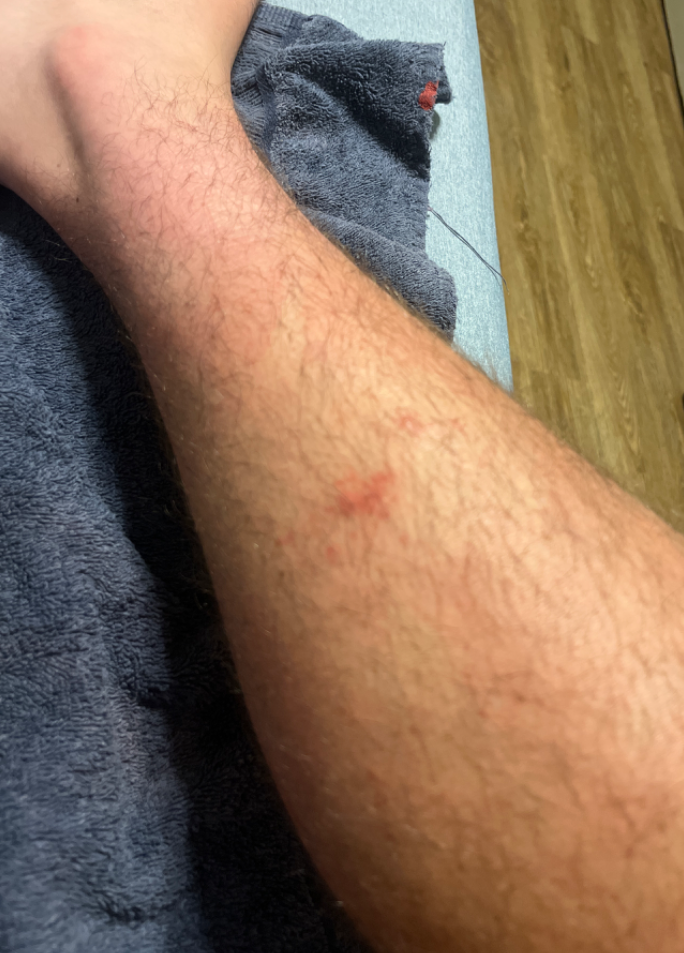Assessment: Diagnostic features were not clearly distinguishable in this photograph. Clinical context: Located on the front of the torso, leg and arm. Present for less than one week. Self-categorized by the patient as a rash. The patient reports the lesion is raised or bumpy and fluid-filled. The lesion is associated with itching. The photo was captured at a distance. Male patient, age 18–29. The patient also reports fatigue.